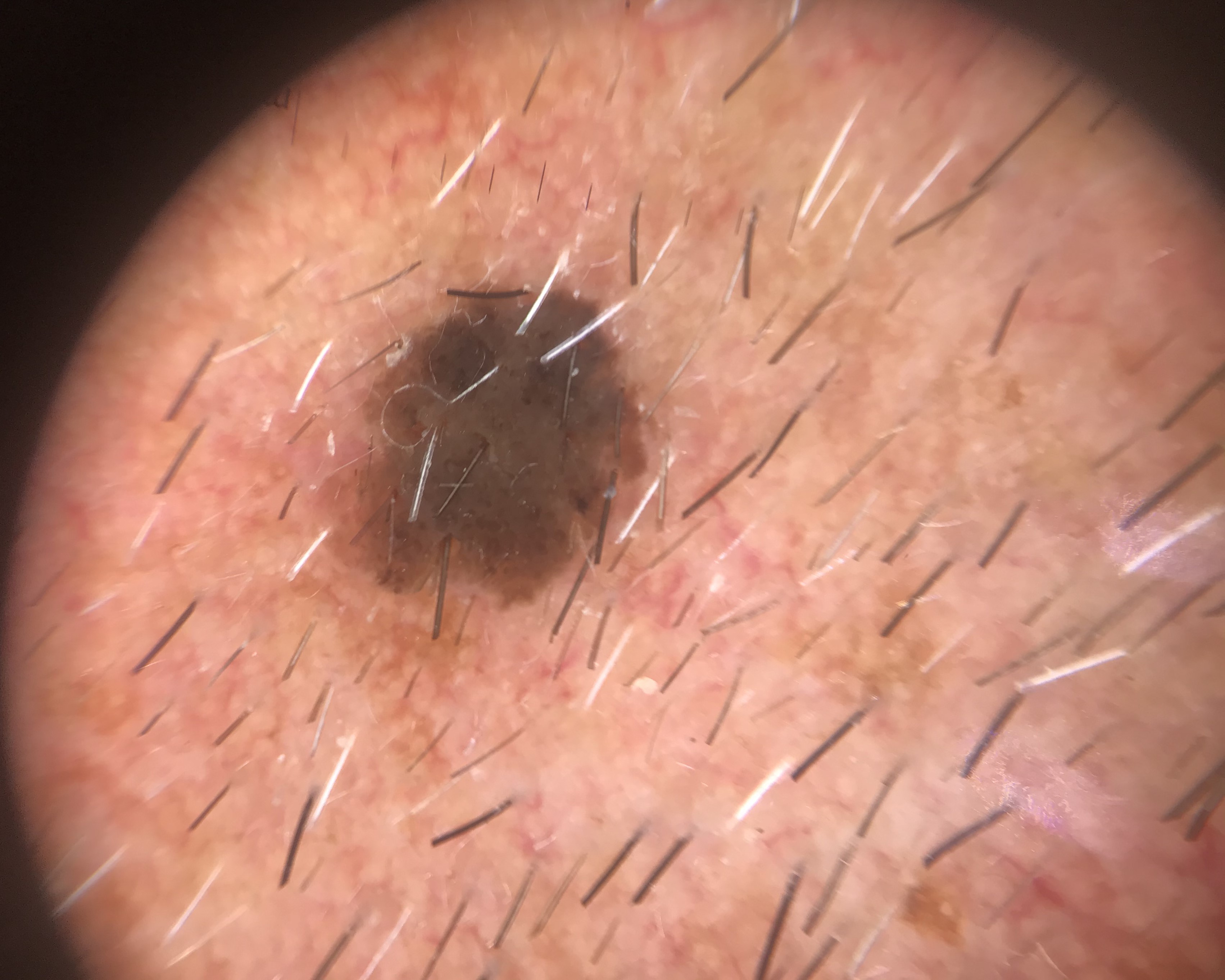| field | value |
|---|---|
| image type | dermoscopy |
| diagnostic label | seborrheic keratosis (expert consensus) |